Located on the back of the torso, front of the torso and head or neck · close-up view: 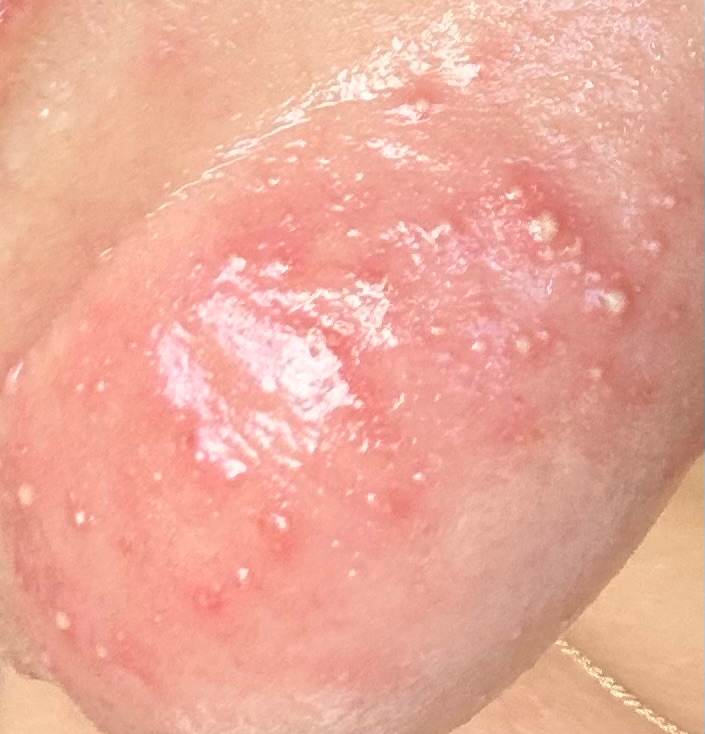The condition has been present for about one day. Fitzpatrick skin type II. The lesion is described as raised or bumpy. On dermatologist assessment of the image: the differential, in no particular order, includes Rosacea and Perioral Dermatitis.